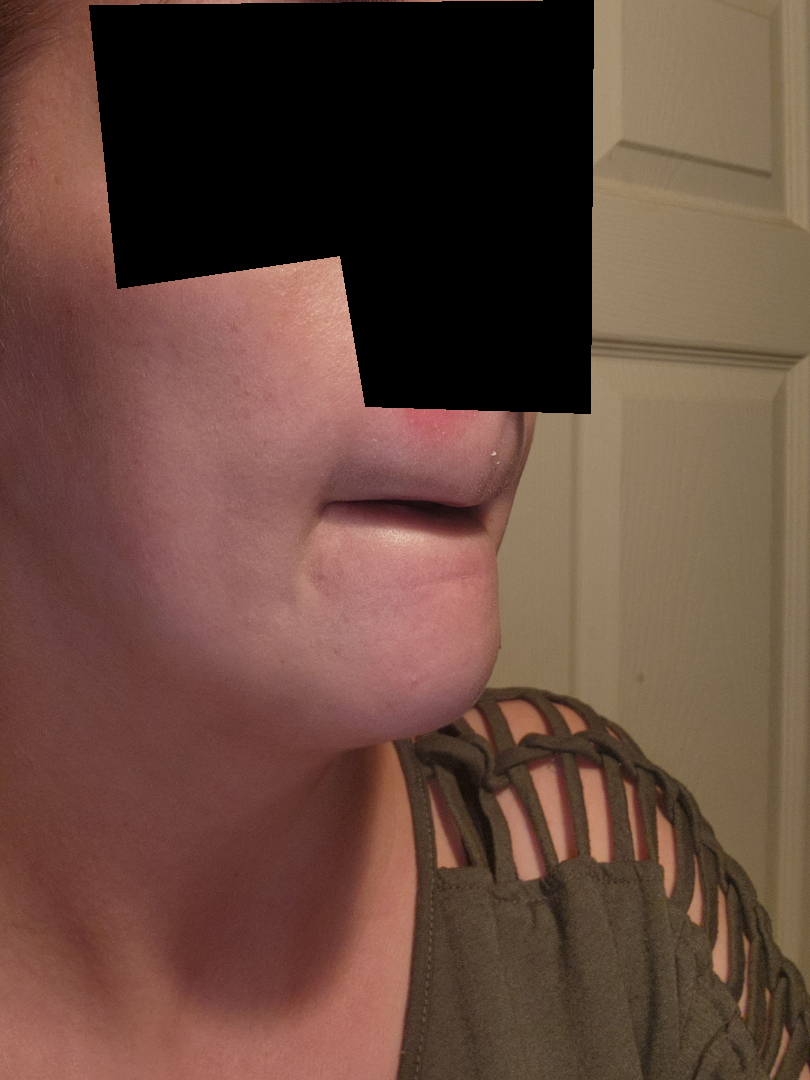The affected area is the head or neck. An image taken at a distance. The contributor is 30–39, female. On teledermatology review, most likely Perioral Dermatitis; lower on the differential is Herpes Simplex; less likely is Seborrheic Dermatitis.